A dermatoscopic image of a skin lesion: 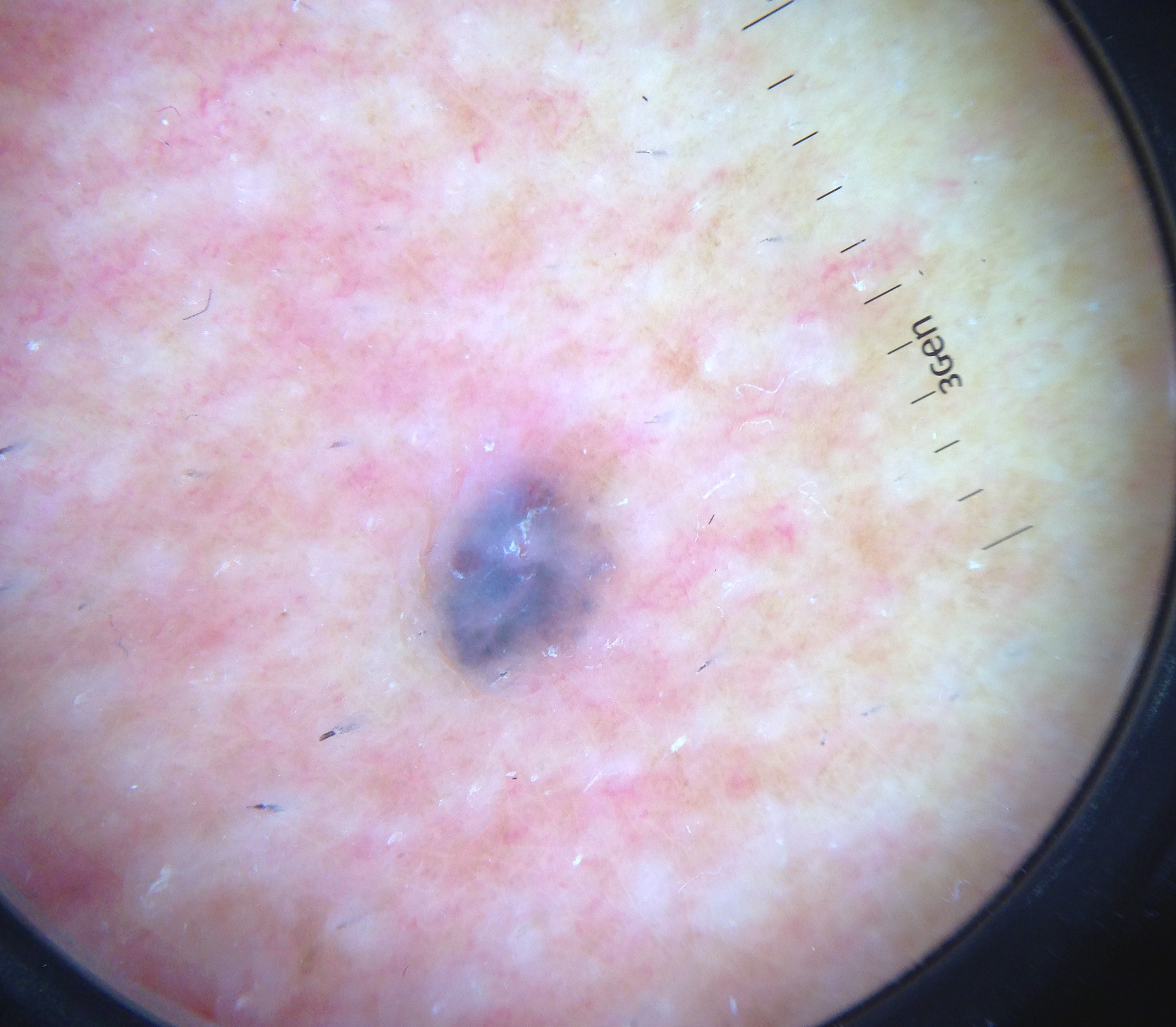Findings:
- lesion type — keratinocytic
- class — basal cell carcinoma (biopsy-proven)